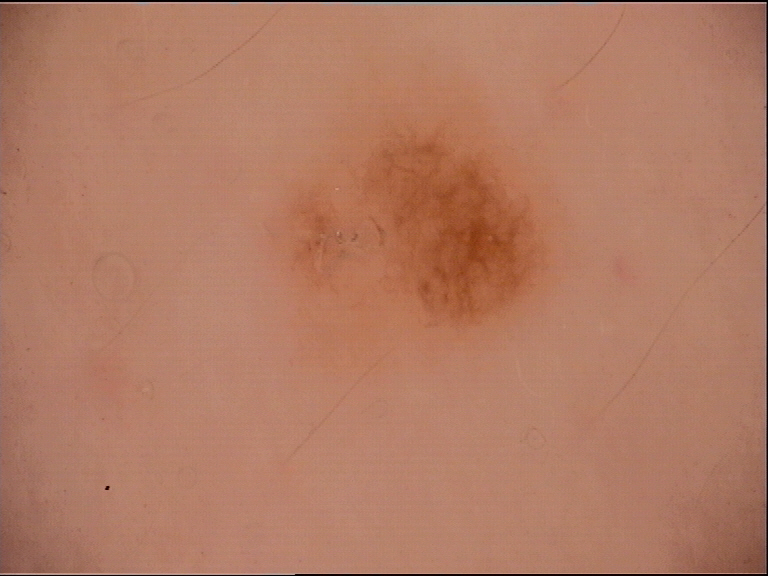A skin lesion imaged with a dermatoscope. This is a banal lesion. The diagnosis was a junctional nevus.